A female subject age 20 · a dermoscopy image of a skin lesion · the patient says their skin reddens with sun exposure.
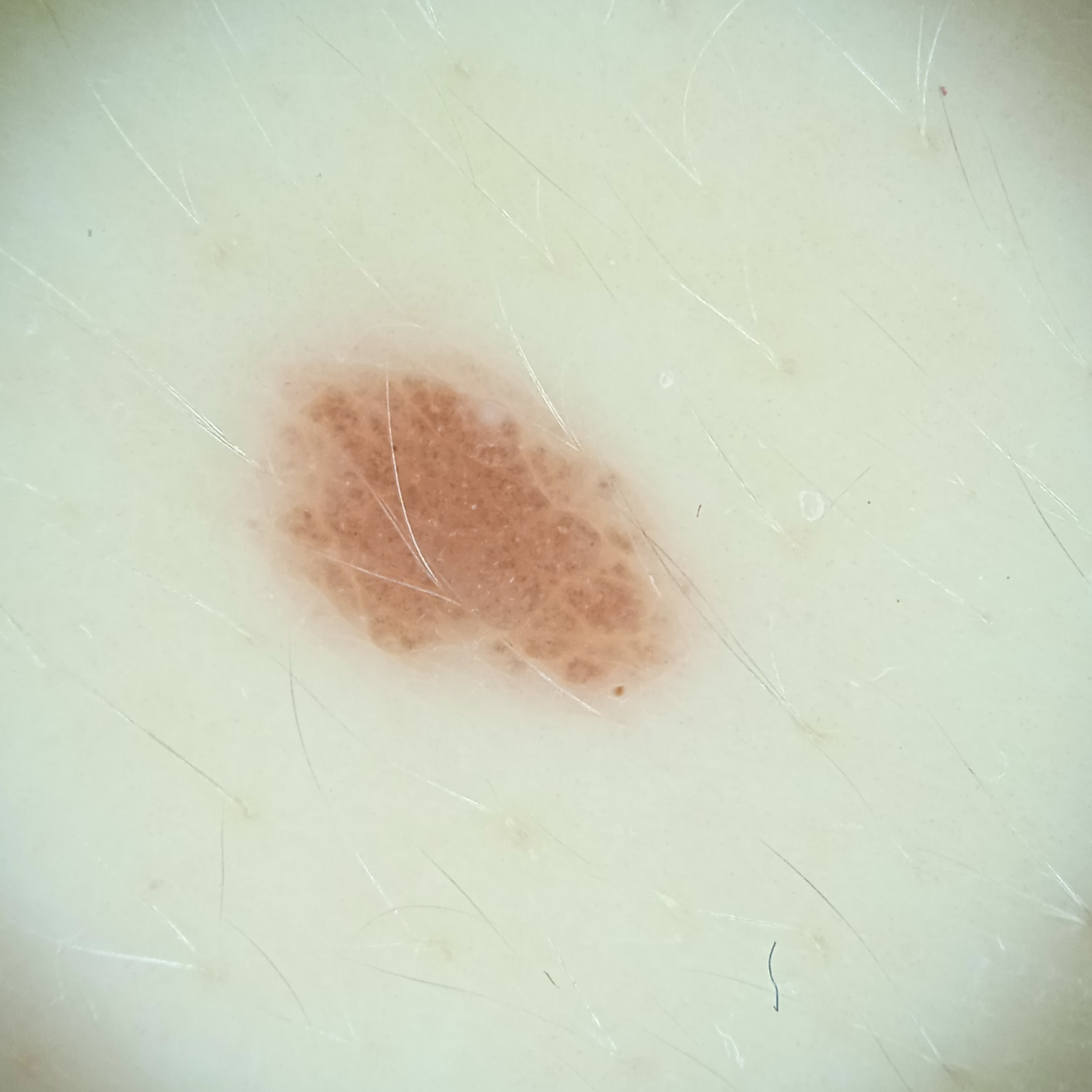| feature | finding |
|---|---|
| site | the torso |
| lesion size | 5.1 mm |
| diagnostic label | melanocytic nevus (dermatologist consensus) |